A dermatoscopic image of a skin lesion.
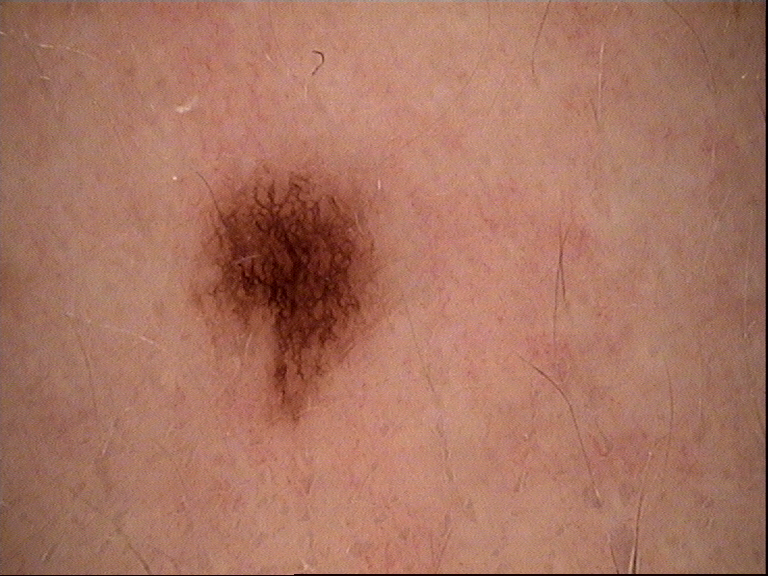Q: What is this lesion?
A: dysplastic junctional nevus (expert consensus)